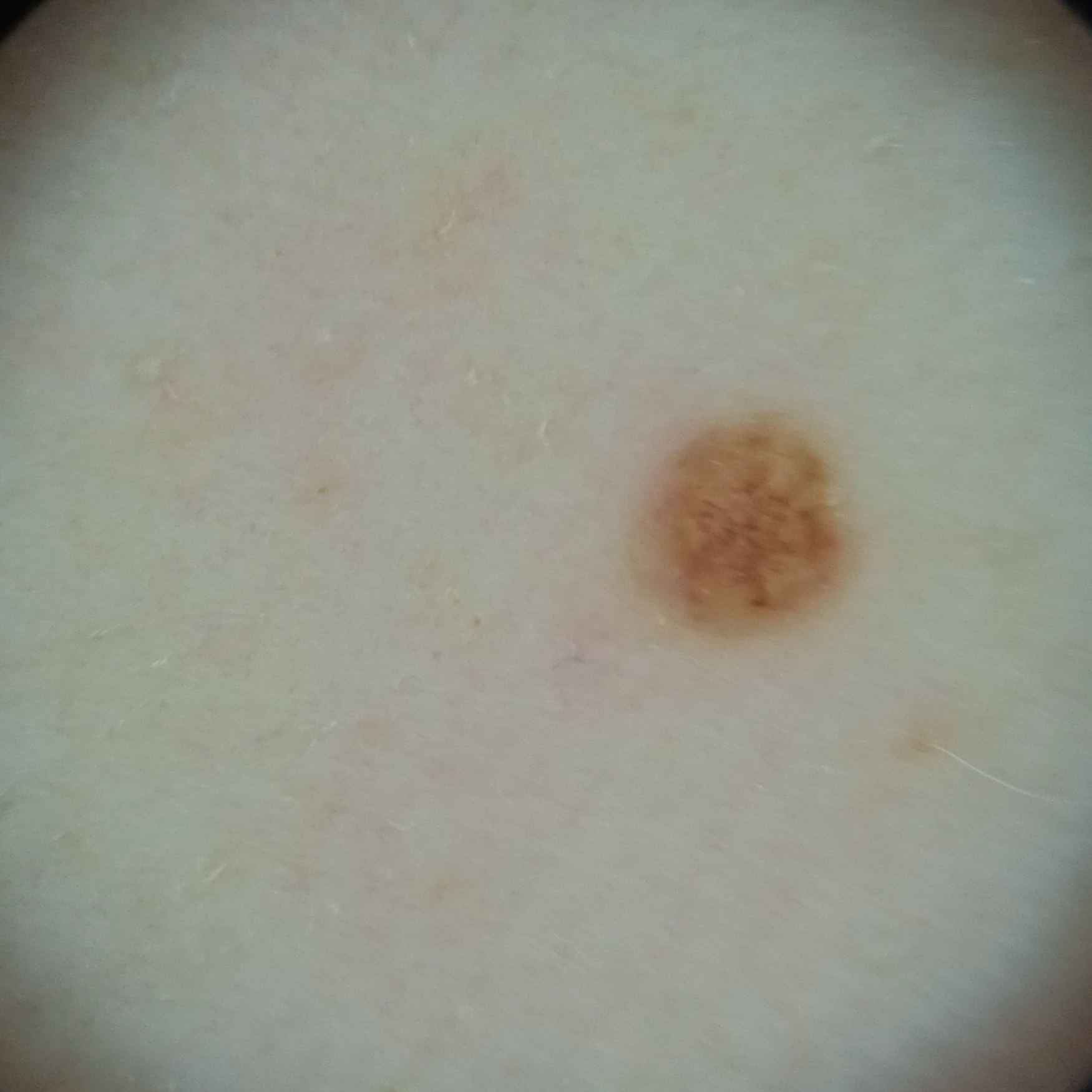The patient describes having a moderate number of moles. A skin lesion imaged with a dermatoscope. The patient says their skin reddens painfully with sun exposure. On a questionnaire the patient reported no personal history of skin cancer. Acquired for a research image collection, with no referral diagnosis. A female patient age 50. Located on the back. The lesion is about 2.2 mm across. The consensus diagnosis for this lesion was a melanocytic nevus.